A male subject in their 80s; a skin lesion imaged with a dermatoscope:
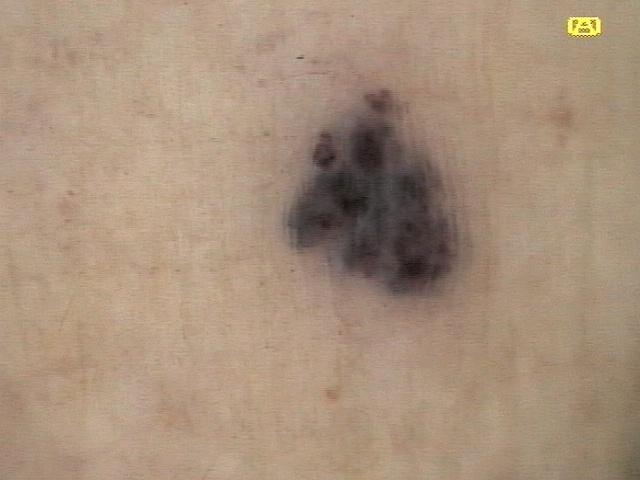• diagnosis · vascular lesion (clinical impression)